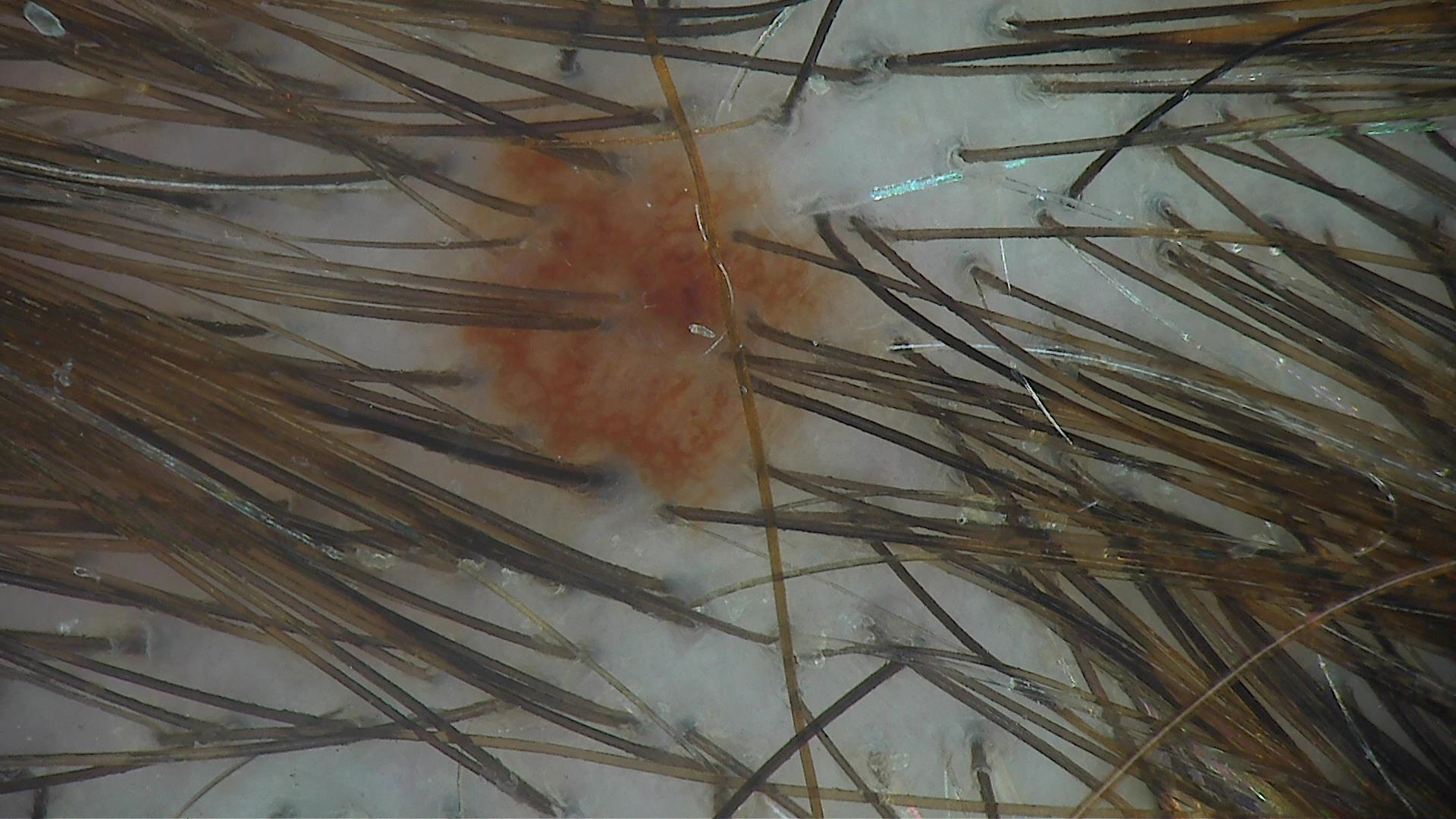Labeled as a dysplastic junctional nevus.